Fitzpatrick phototype III. An image taken at a distance:
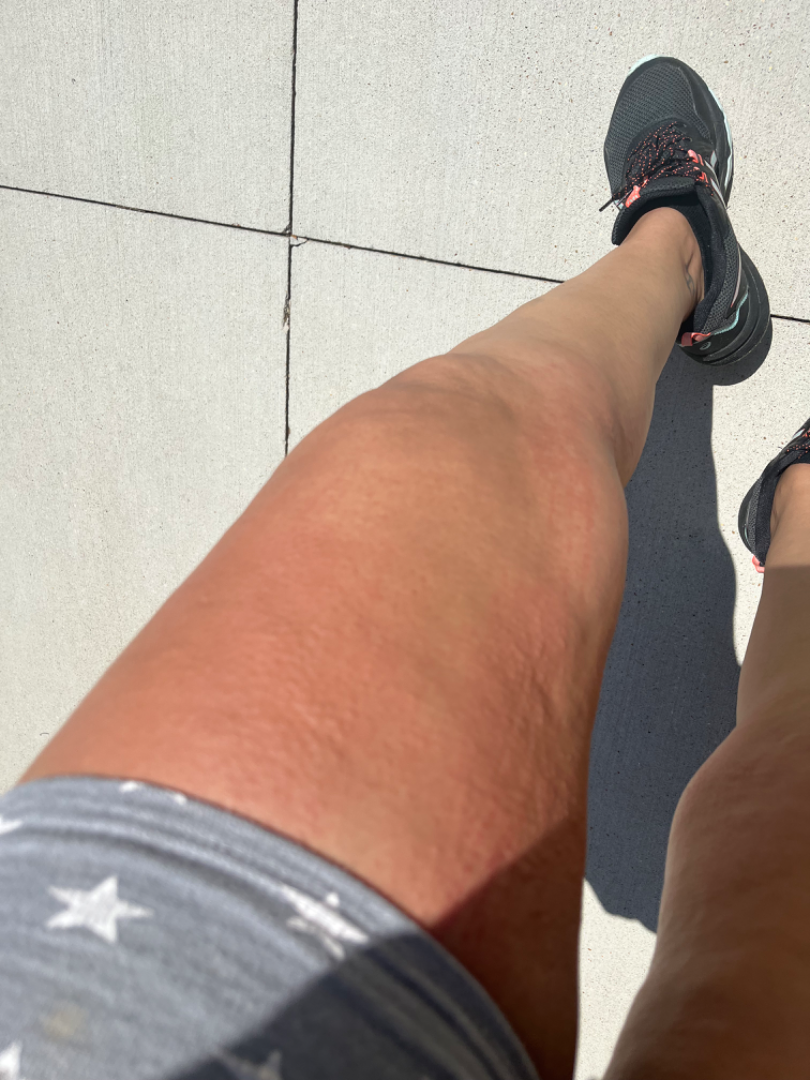assessment = ungradable on photographic review.